A skin lesion imaged with a dermatoscope: 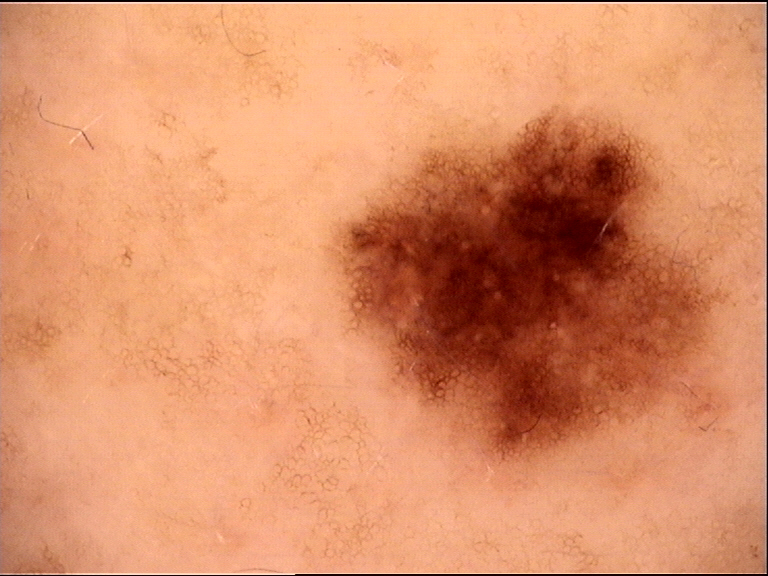Impression: The diagnosis was a benign lesion — a dysplastic junctional nevus.